Reported duration is less than one week · associated systemic symptoms include fatigue · male patient, age 18–29 · the patient reports the lesion is fluid-filled and raised or bumpy · self-categorized by the patient as a rash · close-up view · located on the arm, leg and front of the torso — 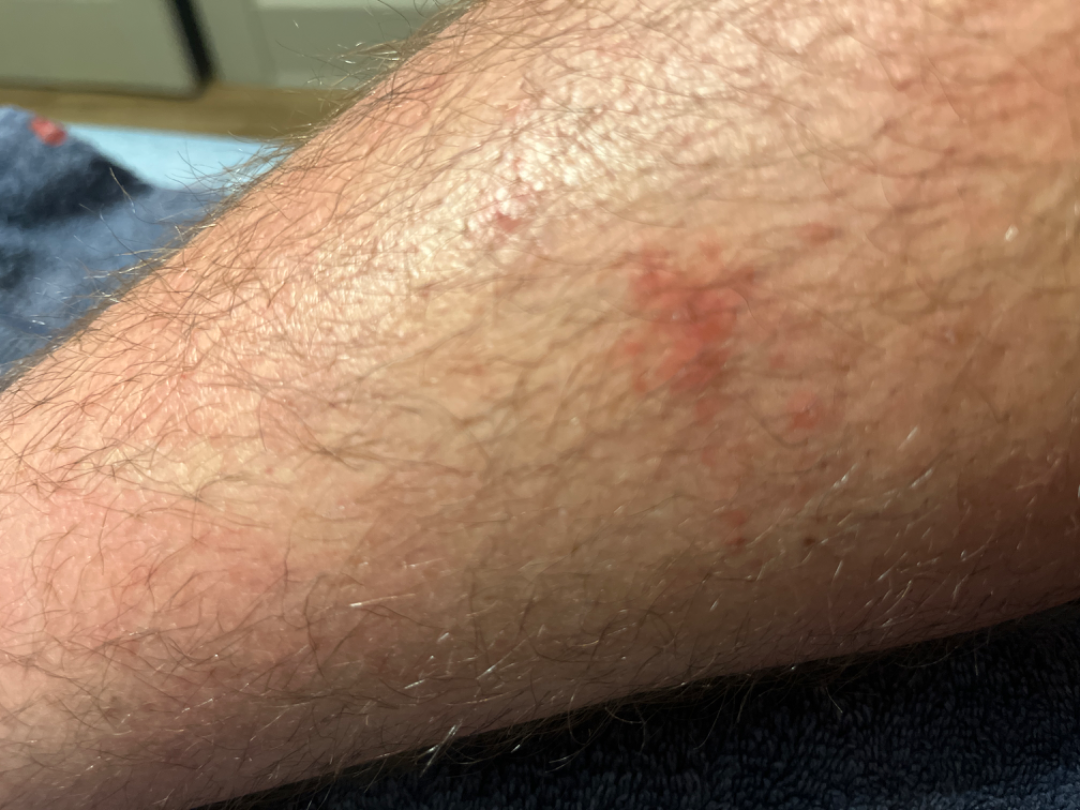Findings:
– assessment · not assessable